The affected area is the back of the torso · this image was taken at an angle.
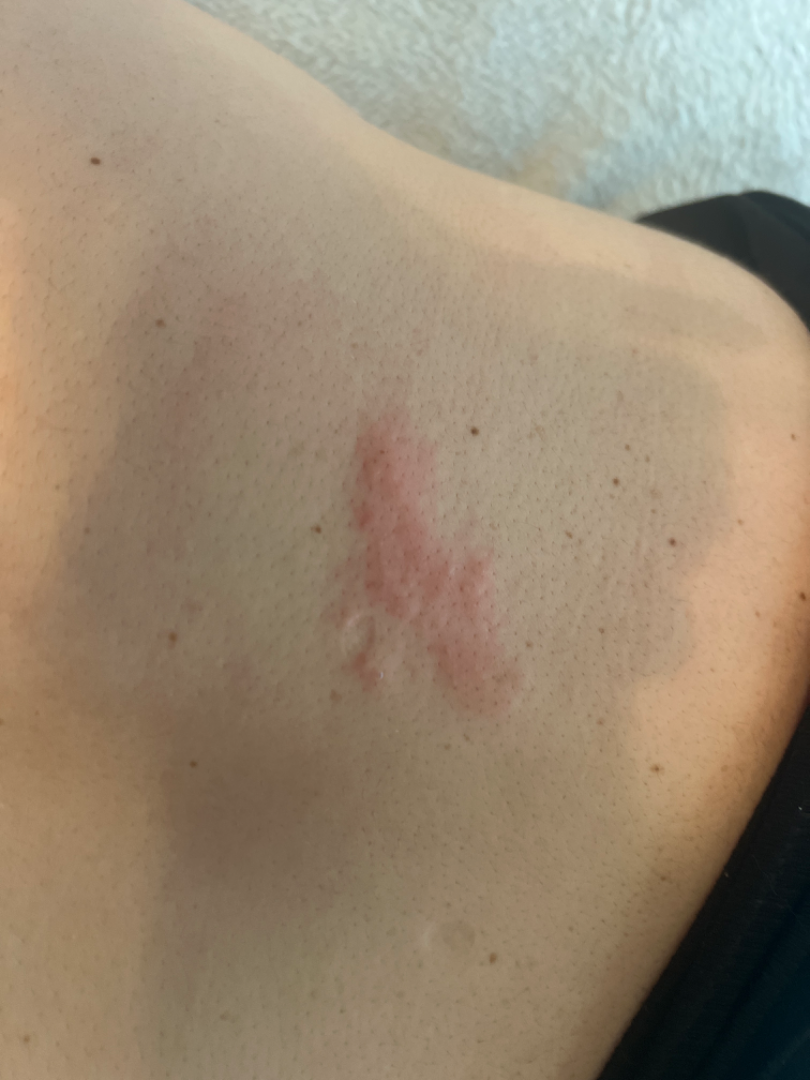Findings:
– assessment — could not be assessed